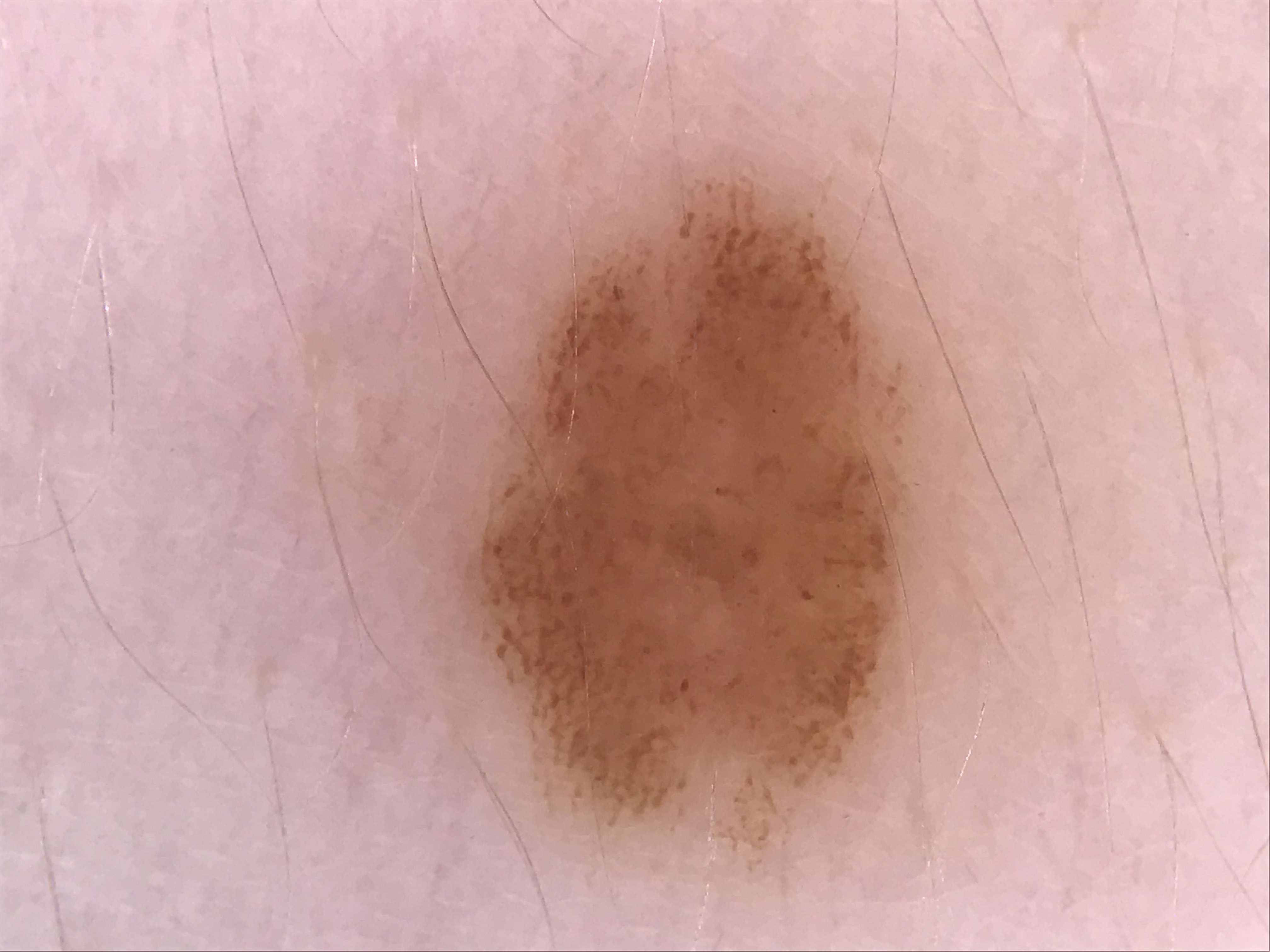The diagnosis was a benign lesion — a dysplastic junctional nevus.